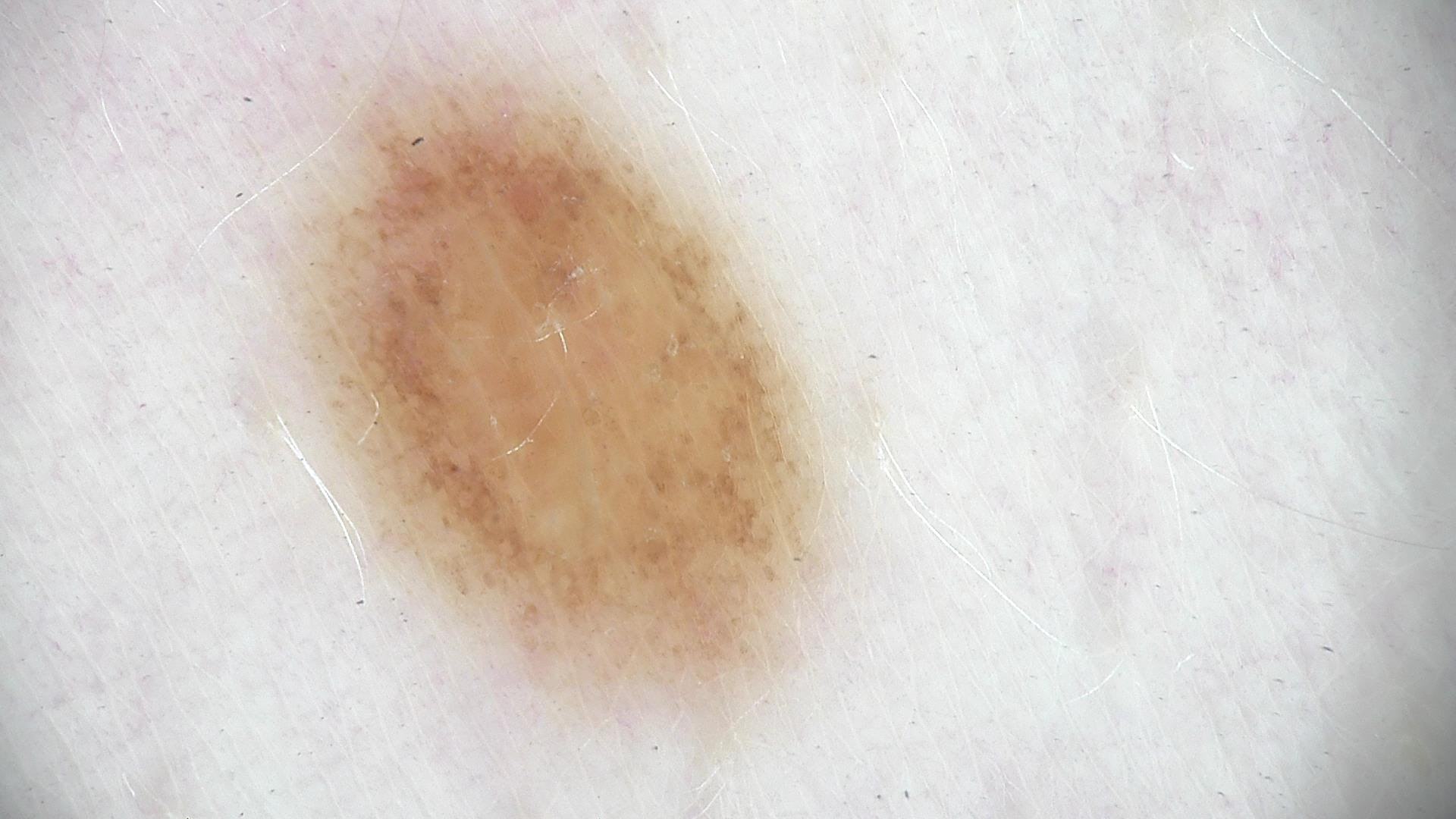Consistent with a compound nevus.